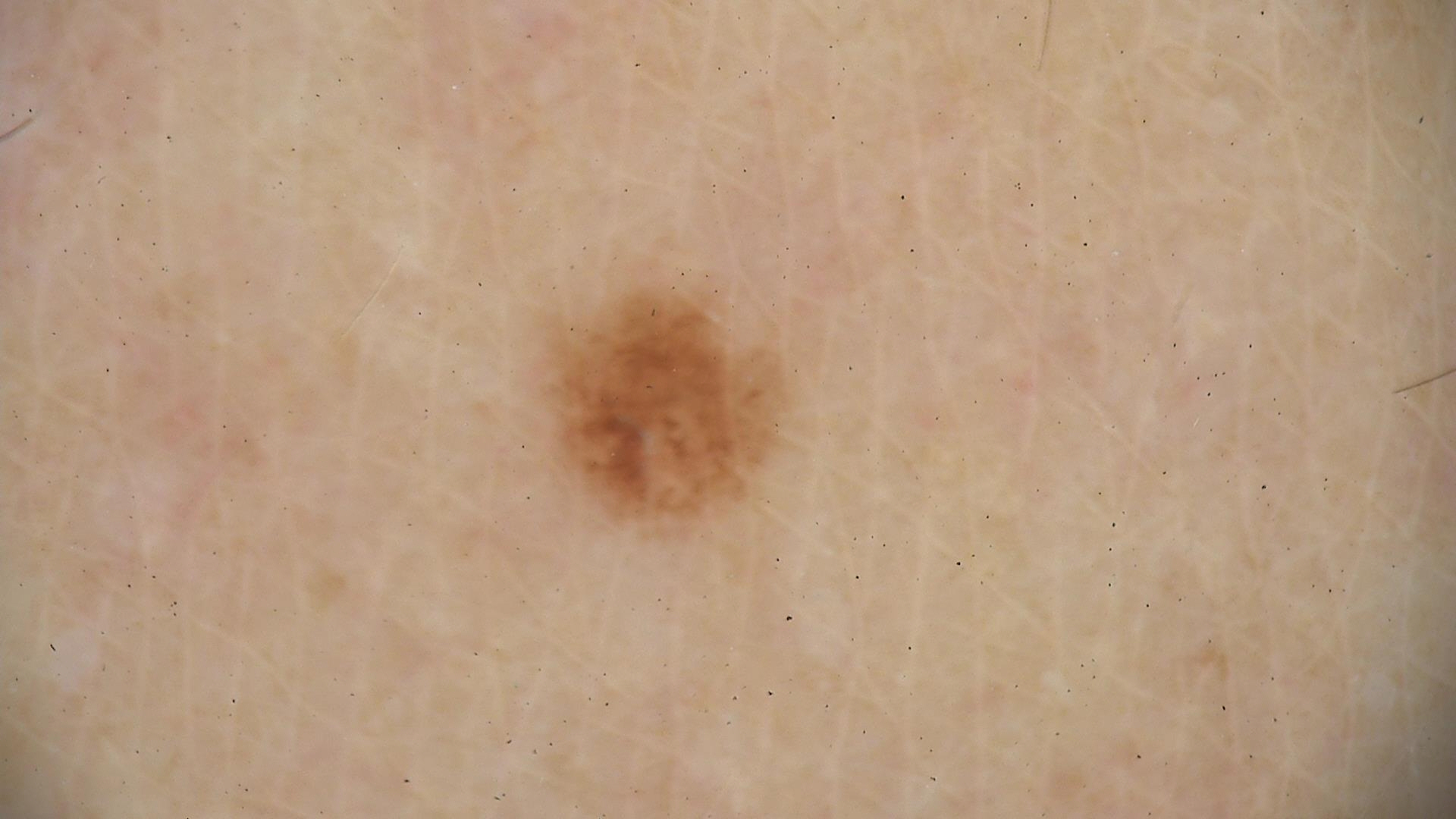imaging: dermatoscopy, label: dysplastic junctional nevus (expert consensus).